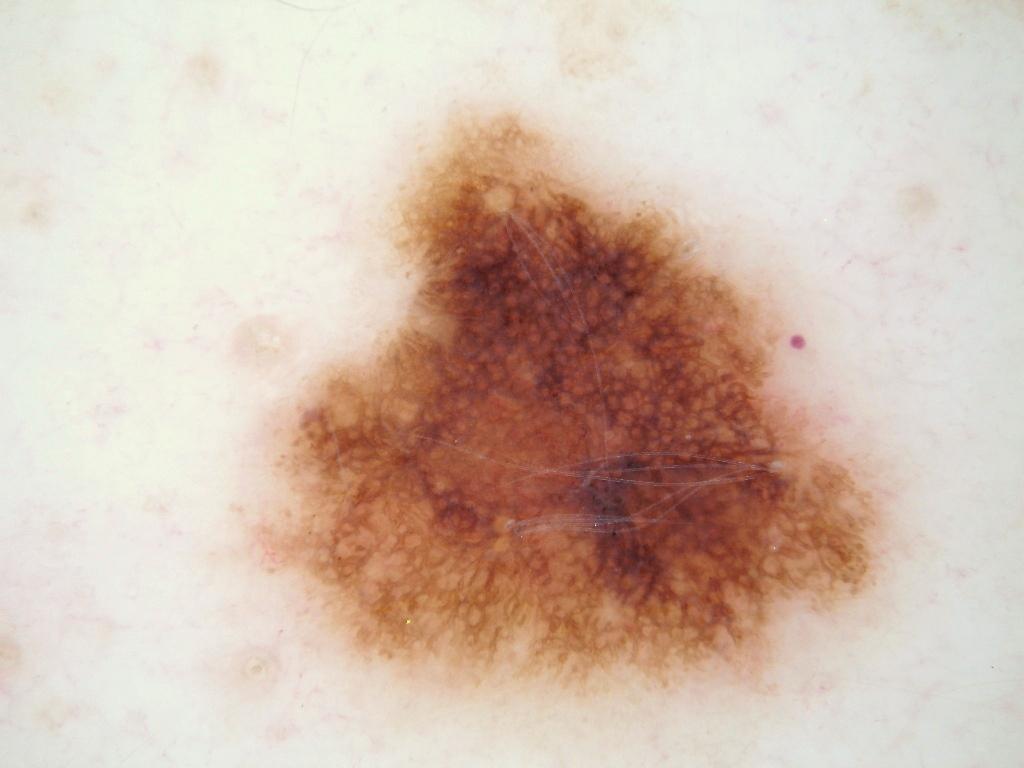patient = male, roughly 50 years of age; image = dermoscopic image; lesion bbox = [254, 115, 892, 695]; extent = ~30% of the field; dermoscopic features = pigment network and globules; impression = a melanocytic nevus.